The patient indicates the lesion is raised or bumpy. The condition has been present for since childhood. Symptoms reported: darkening. The patient is male. Located on the head or neck. The photograph is a close-up of the affected area.
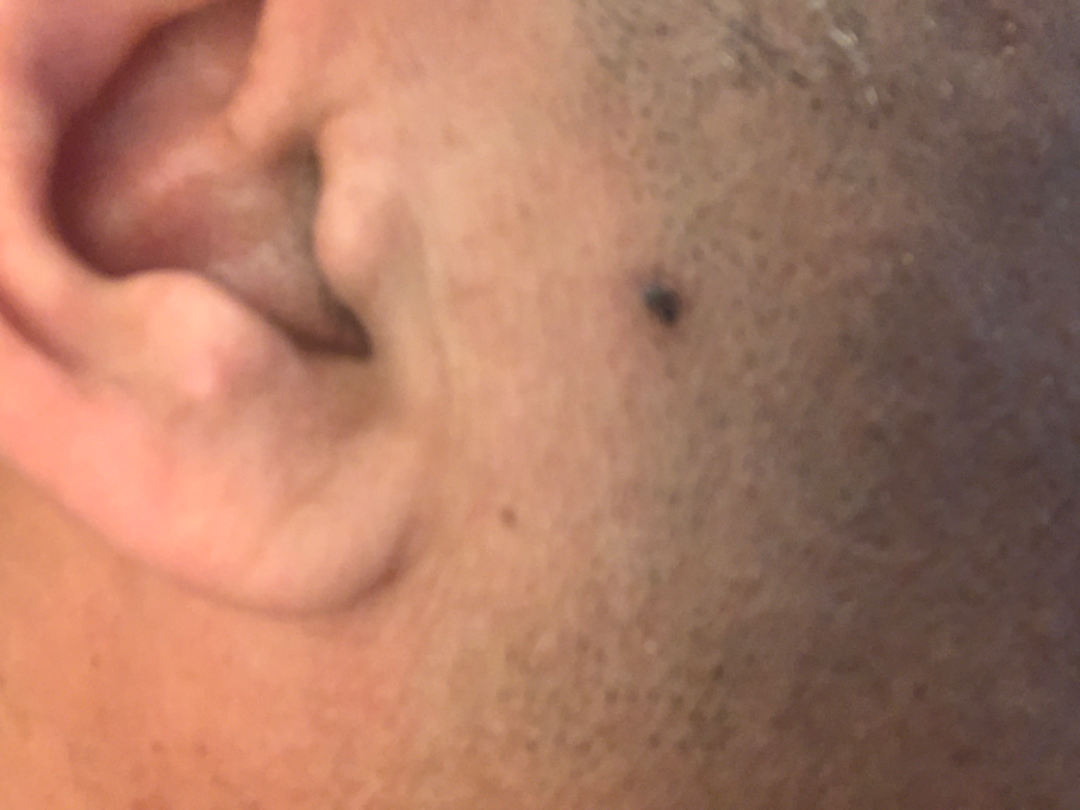Findings:
* assessment · unable to determine